A dermoscopic close-up of a skin lesion: 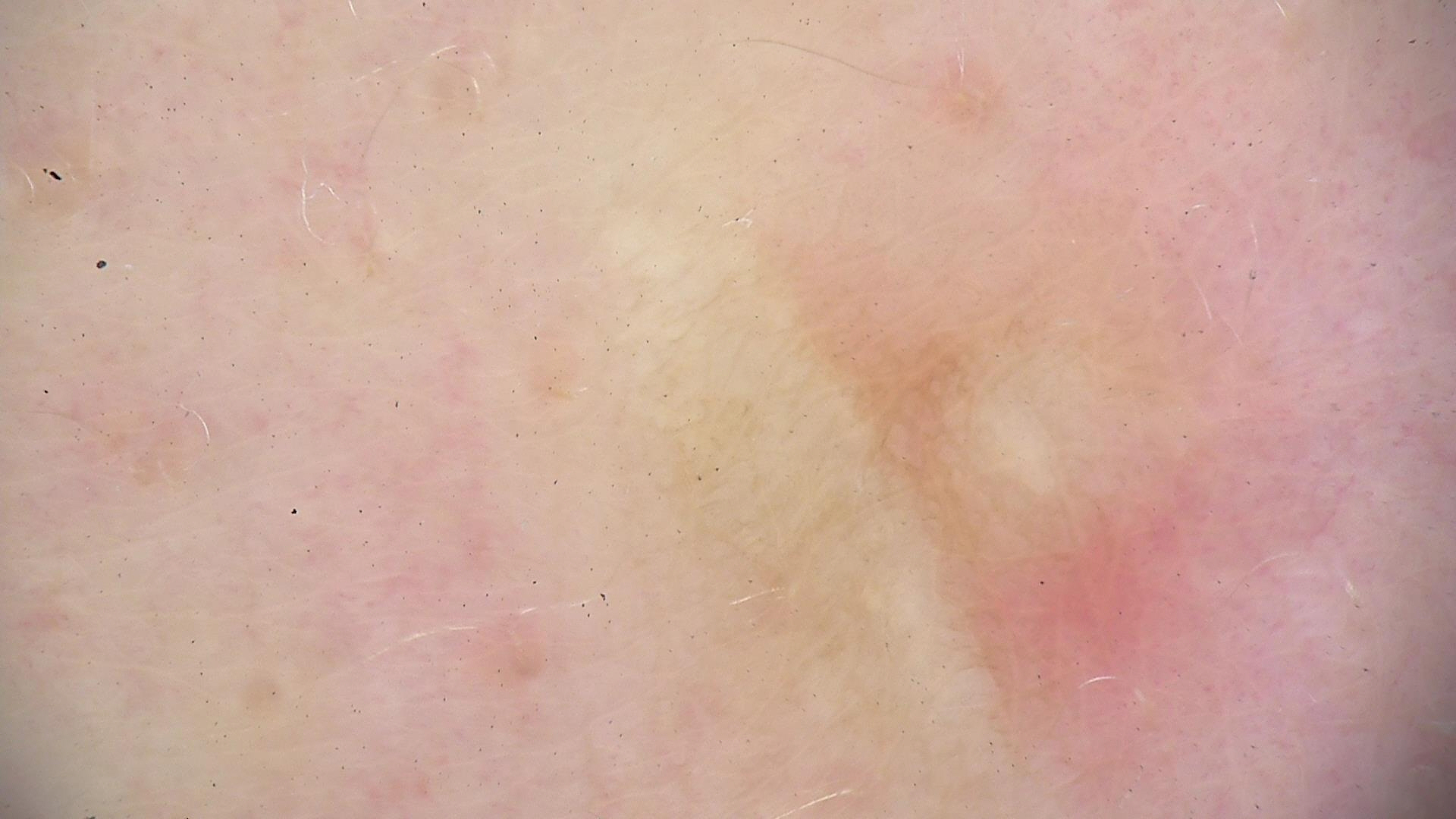Findings: This is a fibro-histiocytic lesion. Conclusion: Classified as a dermatofibroma.